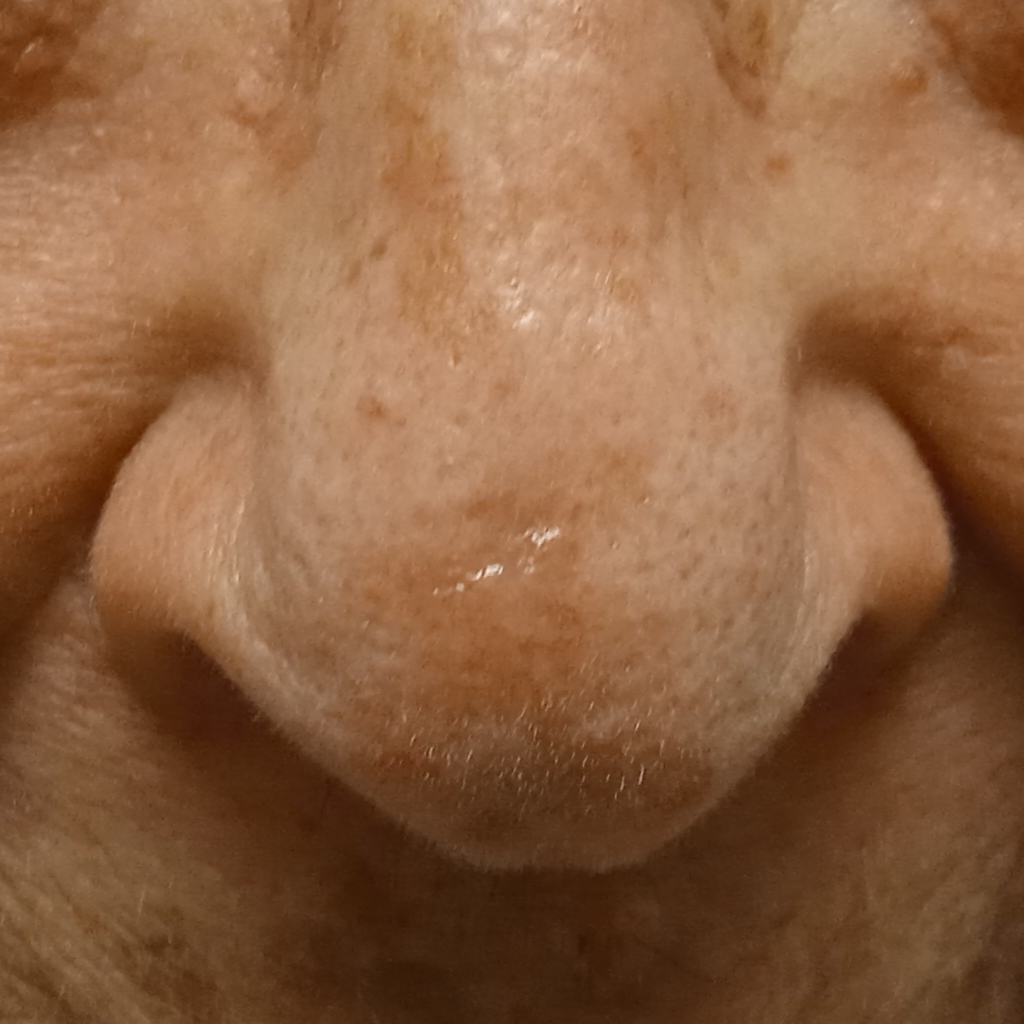The patient reports a personal history of cancer and no personal history of skin cancer. Few moles overall by the patient's own estimate. Referred for assessment of suspected basal cell carcinoma. A macroscopic clinical photograph of a skin lesion. Histopathology confirmed a basal cell carcinoma, following excision, with a measured tumor thickness of 1.5 mm.